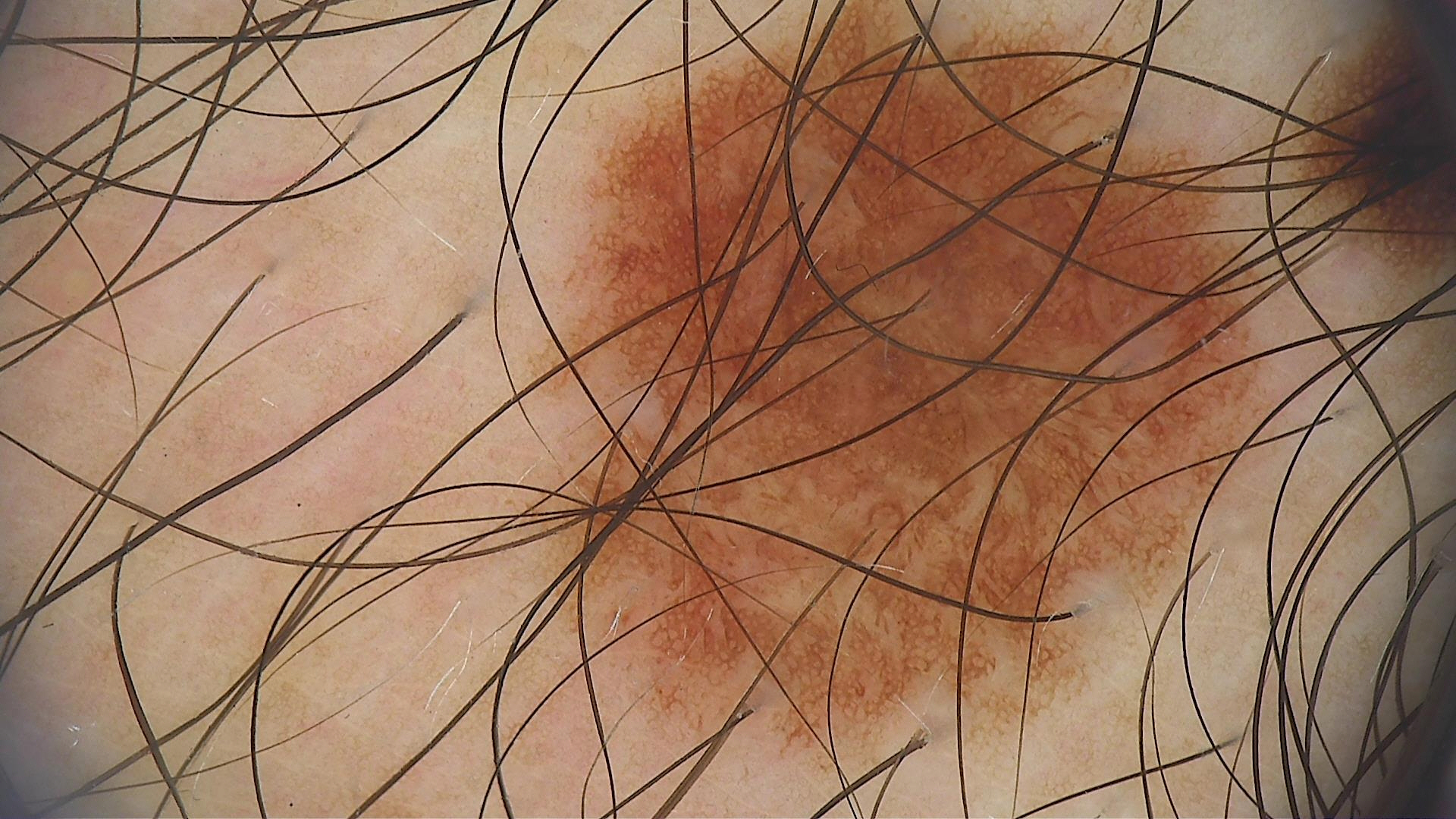modality — dermoscopy
diagnosis — dysplastic junctional nevus (expert consensus)